A skin lesion imaged with a dermatoscope: 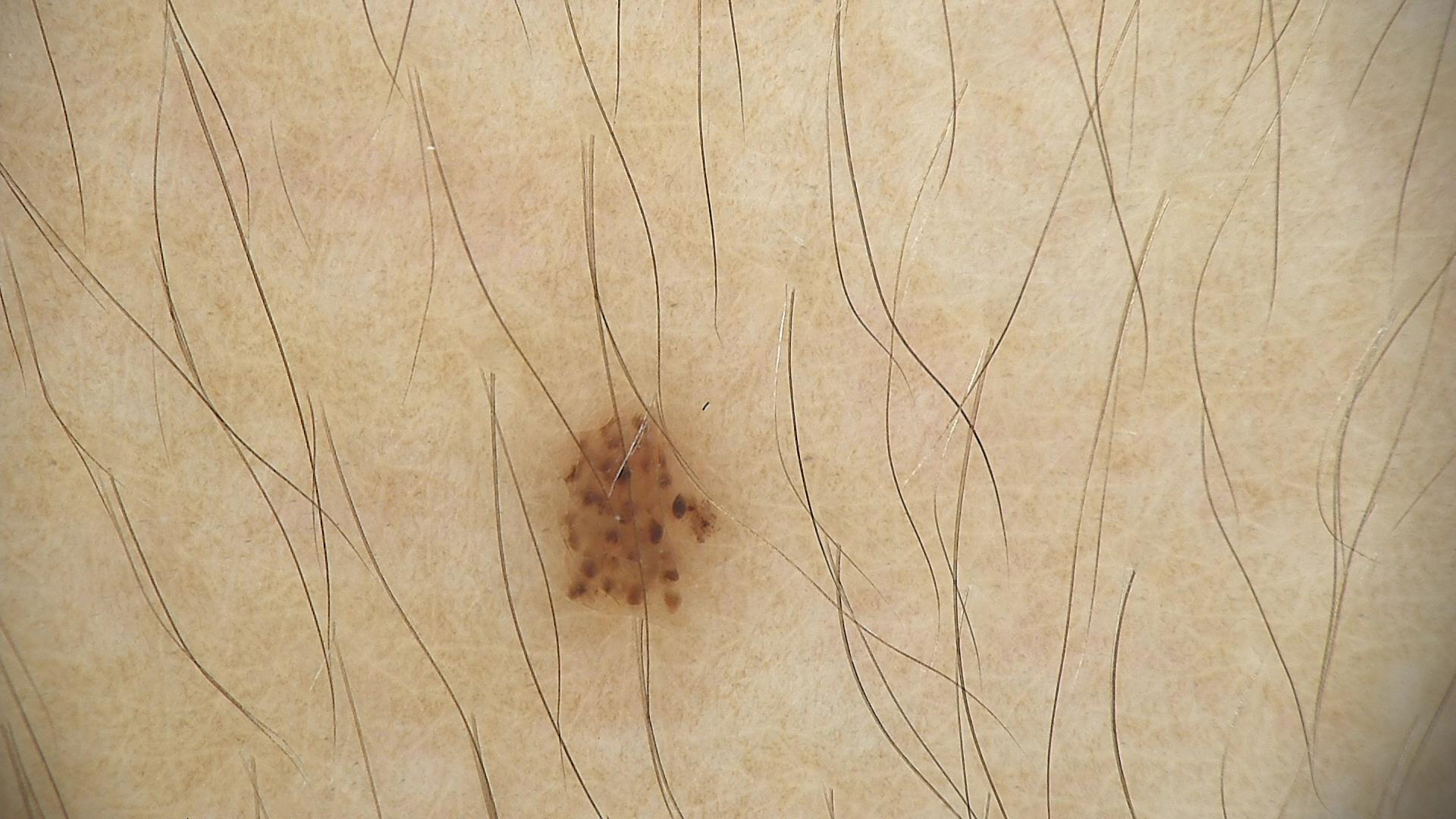Impression: Consistent with a benign lesion — a dysplastic junctional nevus.